A female patient, in their 60s; a dermoscopic view of a skin lesion.
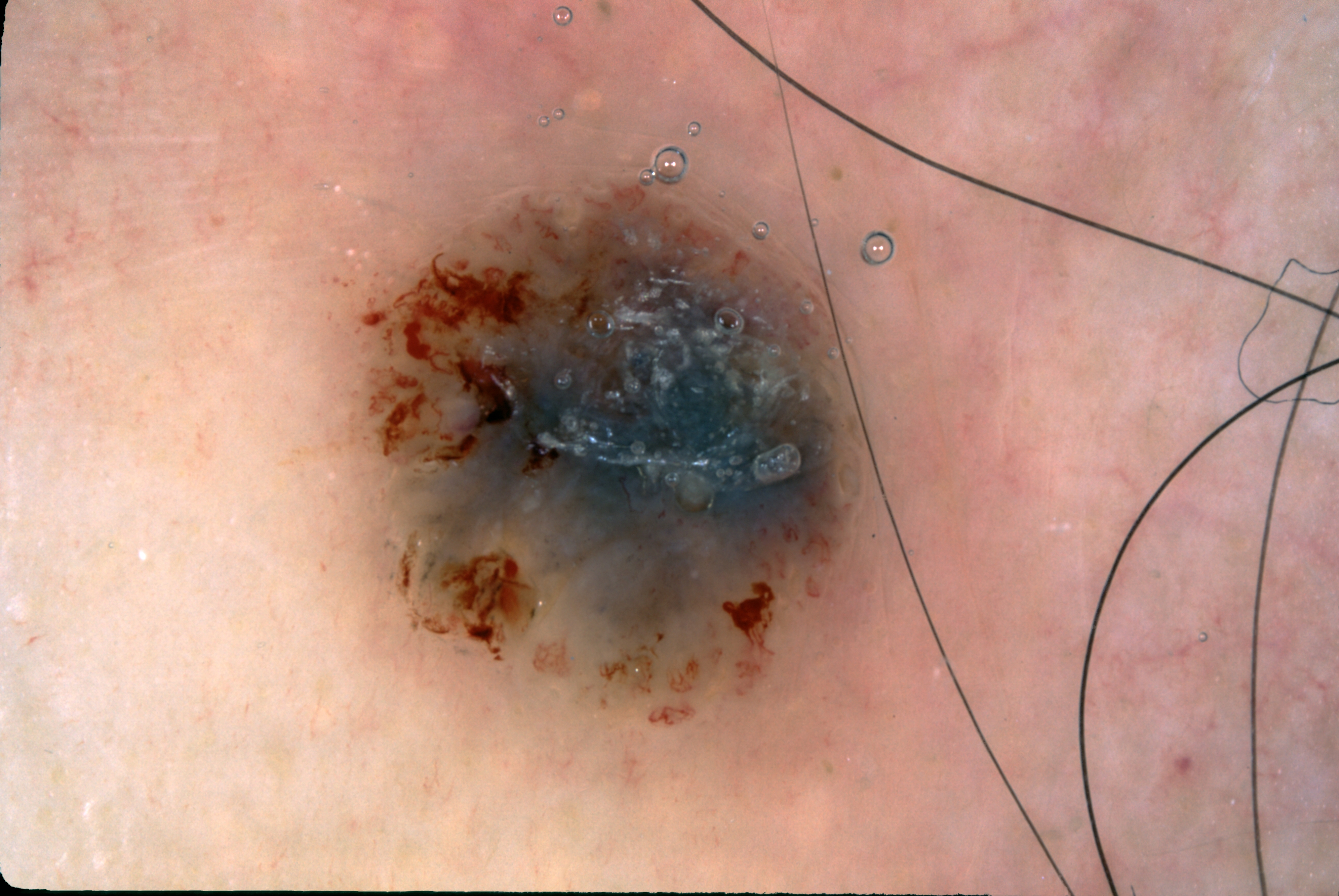The lesion occupies roughly 22% of the field. In (x1, y1, x2, y2) order, lesion location: box(345, 154, 942, 735). Dermoscopy demonstrates milia-like cysts. Diagnosed as a seborrheic keratosis, a benign lesion.